A skin lesion imaged with a dermatoscope: 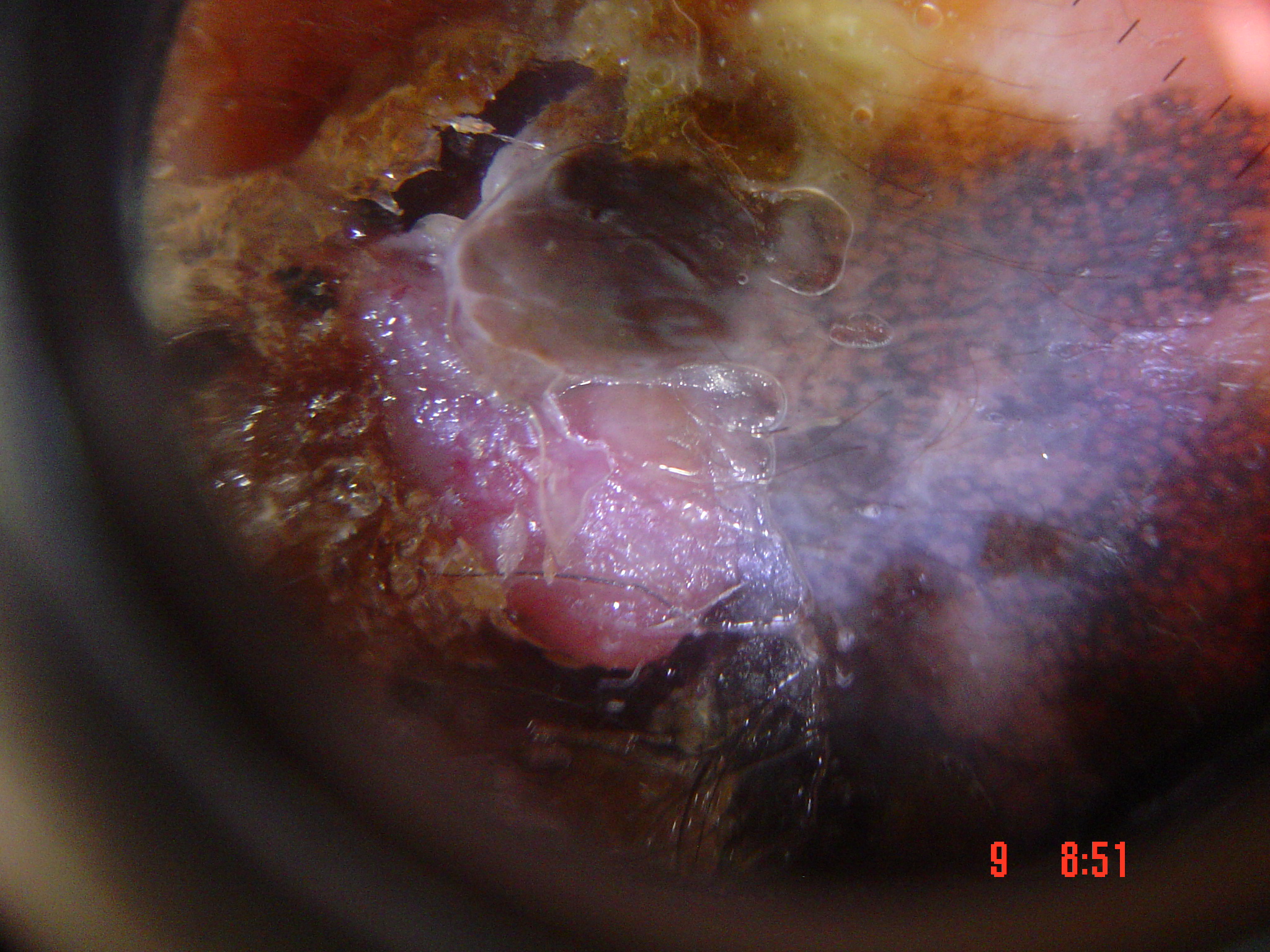label: lentigo maligna melanoma (biopsy-proven).